The condition has been present for less than one week · the affected area is the front of the torso and head or neck · skin tone: FST III · texture is reported as flat · the photograph was taken at a distance · the patient considered this a rash — 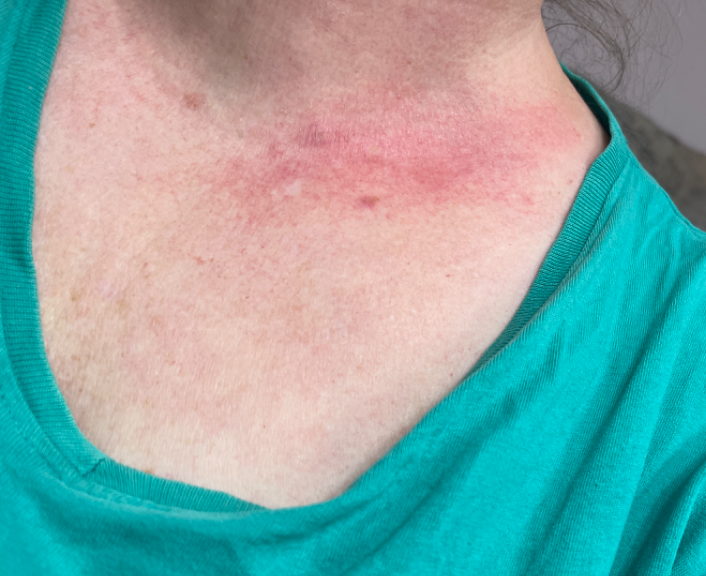{
  "differential": {
    "tied_lead": [
      "Folliculitis",
      "Eczema"
    ],
    "unlikely": [
      "Irritant Contact Dermatitis"
    ]
  }
}